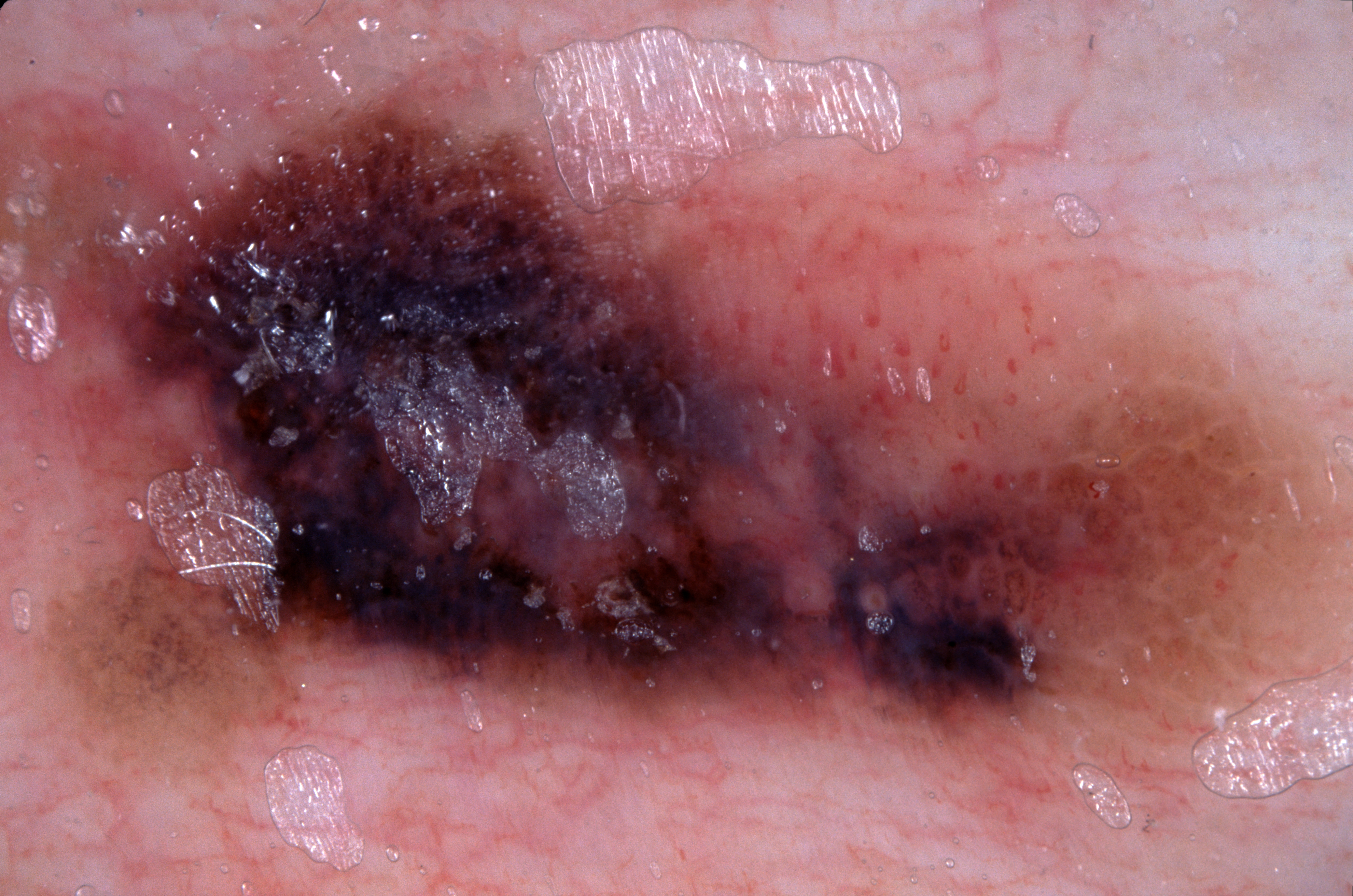| key | value |
|---|---|
| modality | dermoscopy of a skin lesion |
| location | extends across the entire field of view |
| diagnostic label | a melanoma |